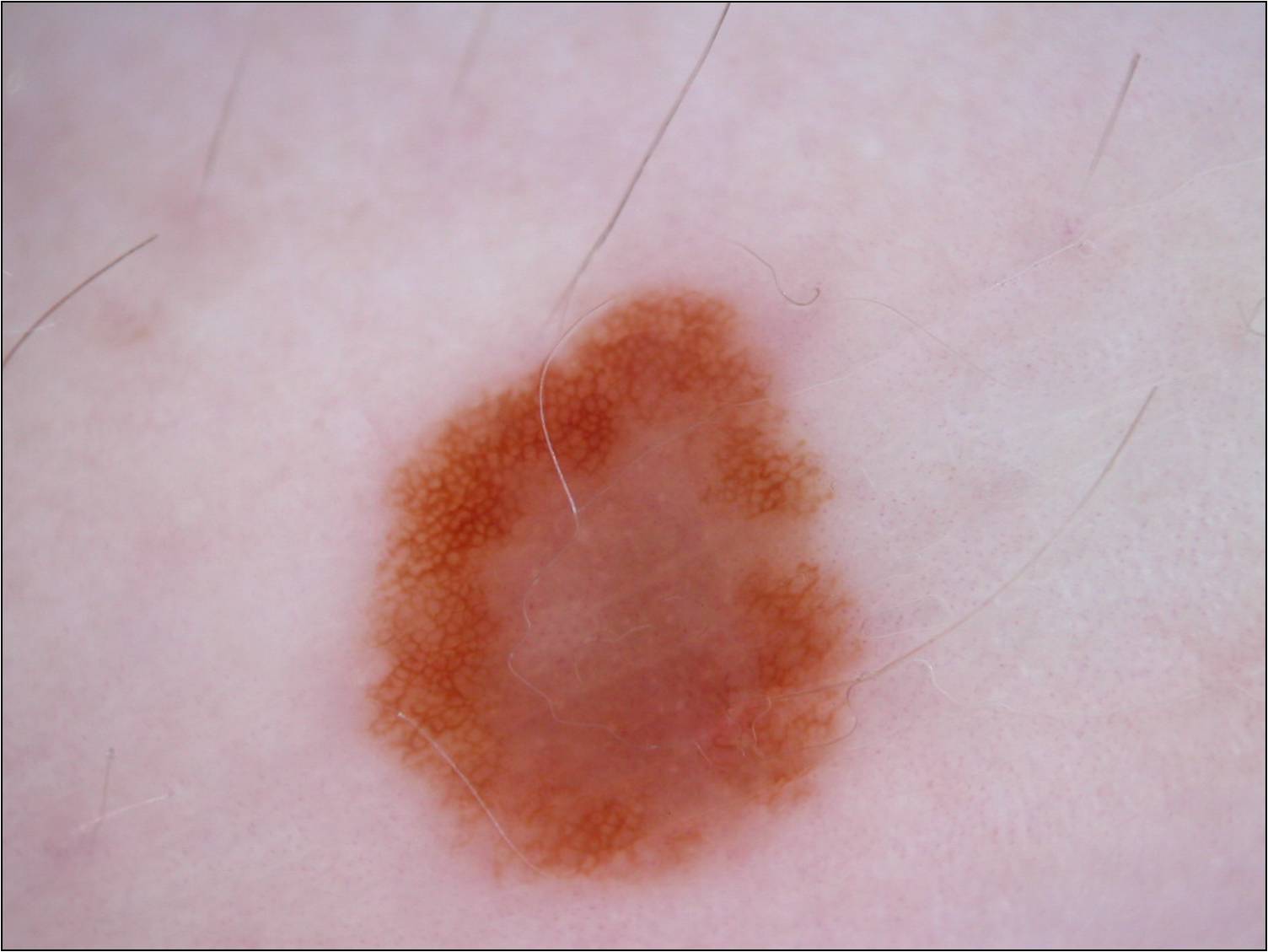A dermatoscopic image of a skin lesion. A female patient, roughly 40 years of age. In (x1, y1, x2, y2) order, the lesion spans 352, 282, 875, 898. A mid-sized lesion within the field. On dermoscopy, the lesion shows pigment network. Diagnosed as a melanocytic nevus, a benign skin lesion.